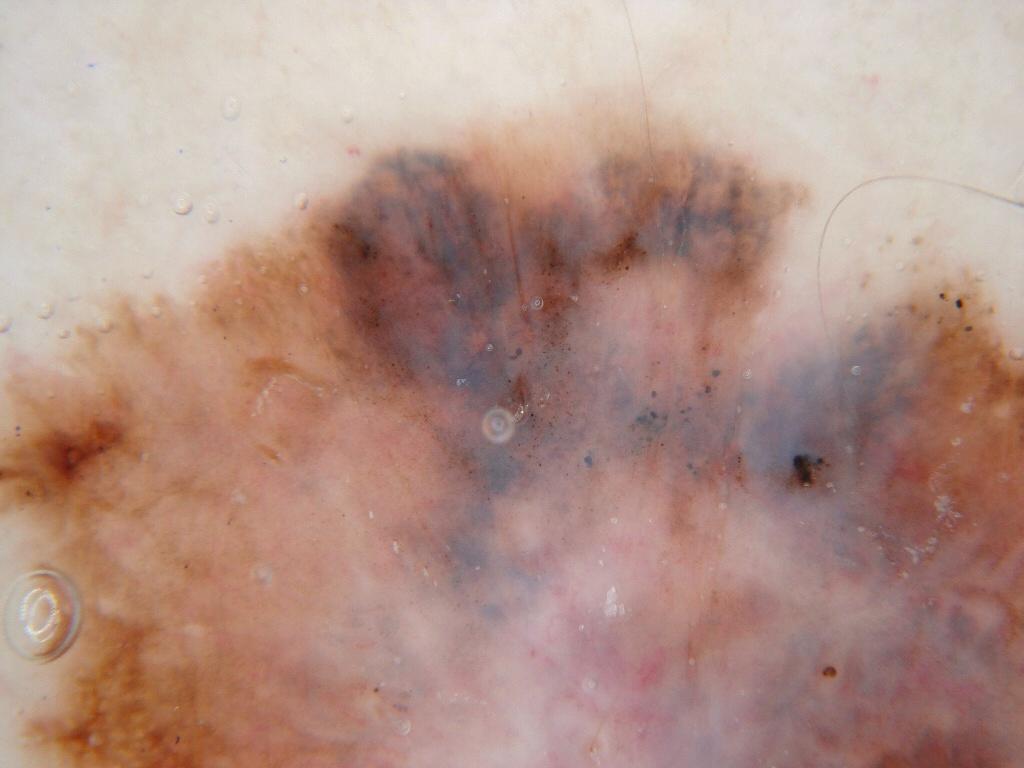imaging — dermoscopy; lesion location — spans the dermoscopic field; assessment — a malignant lesion.